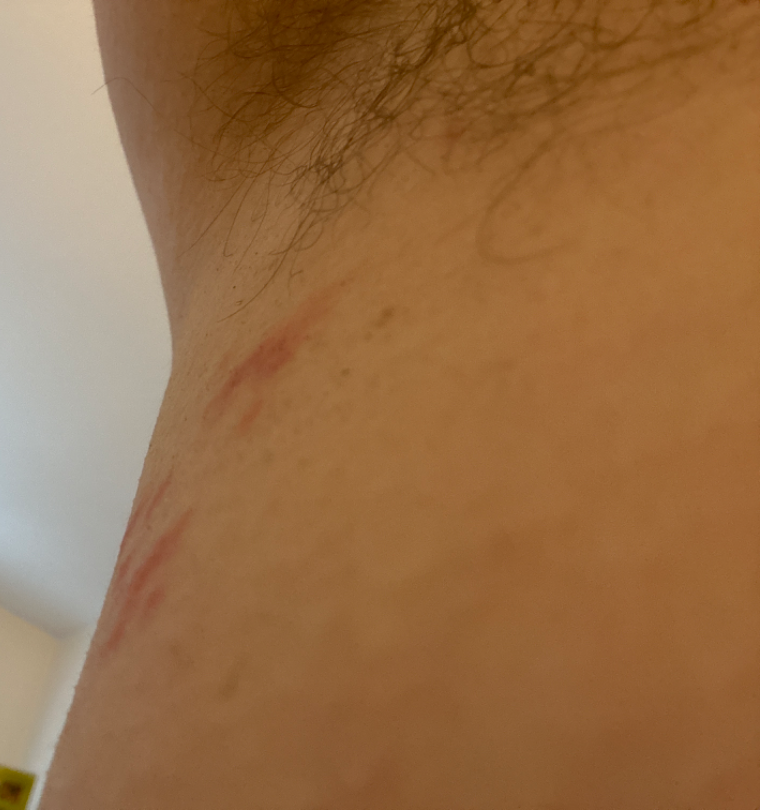Clinical context: The photo was captured at an angle. Fitzpatrick skin type II; lay graders estimated a MST of 2. Assessment: On photographic review, most likely Folliculitis; an alternative is Irritant Contact Dermatitis; also consider Herpes Simplex.